The affected area is the leg. The patient is 18–29, female. The patient considered this a rash. Skin tone: self-reported FST III; lay reviewers estimated Monk skin tone scale 3 (US pool) or 2 (India pool). This image was taken at an angle. No relevant systemic symptoms.
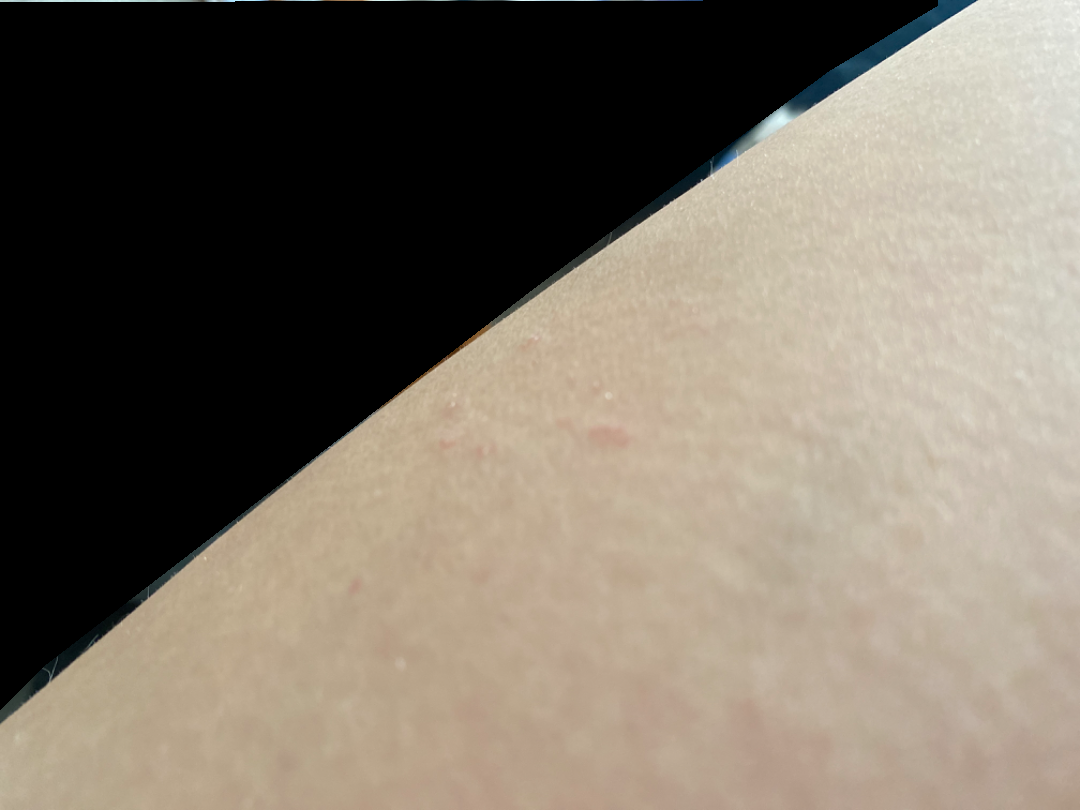{
  "assessment": "unable to determine"
}